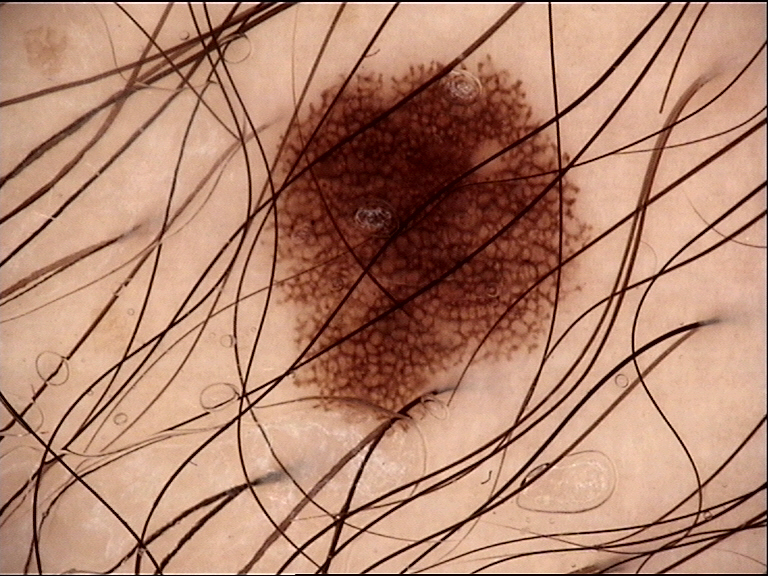Summary: A dermoscopic image of a skin lesion. Impression: Labeled as a dysplastic junctional nevus.